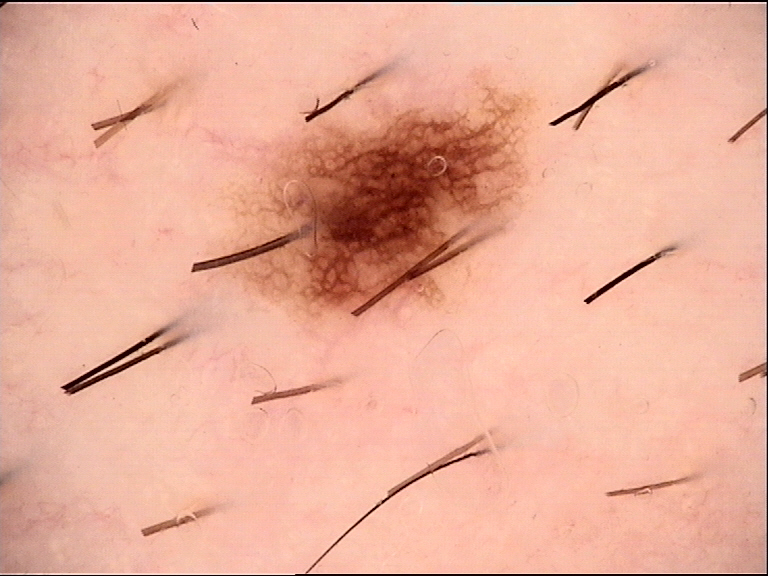A dermoscopic photograph of a skin lesion.
The diagnostic label was a dysplastic junctional nevus.